A dermoscopy image of a single skin lesion.
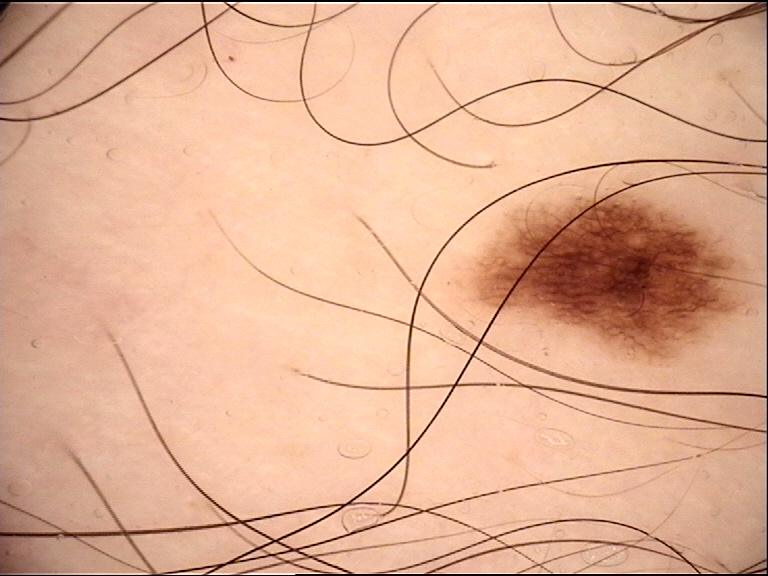Classified as a benign lesion — a dysplastic junctional nevus.